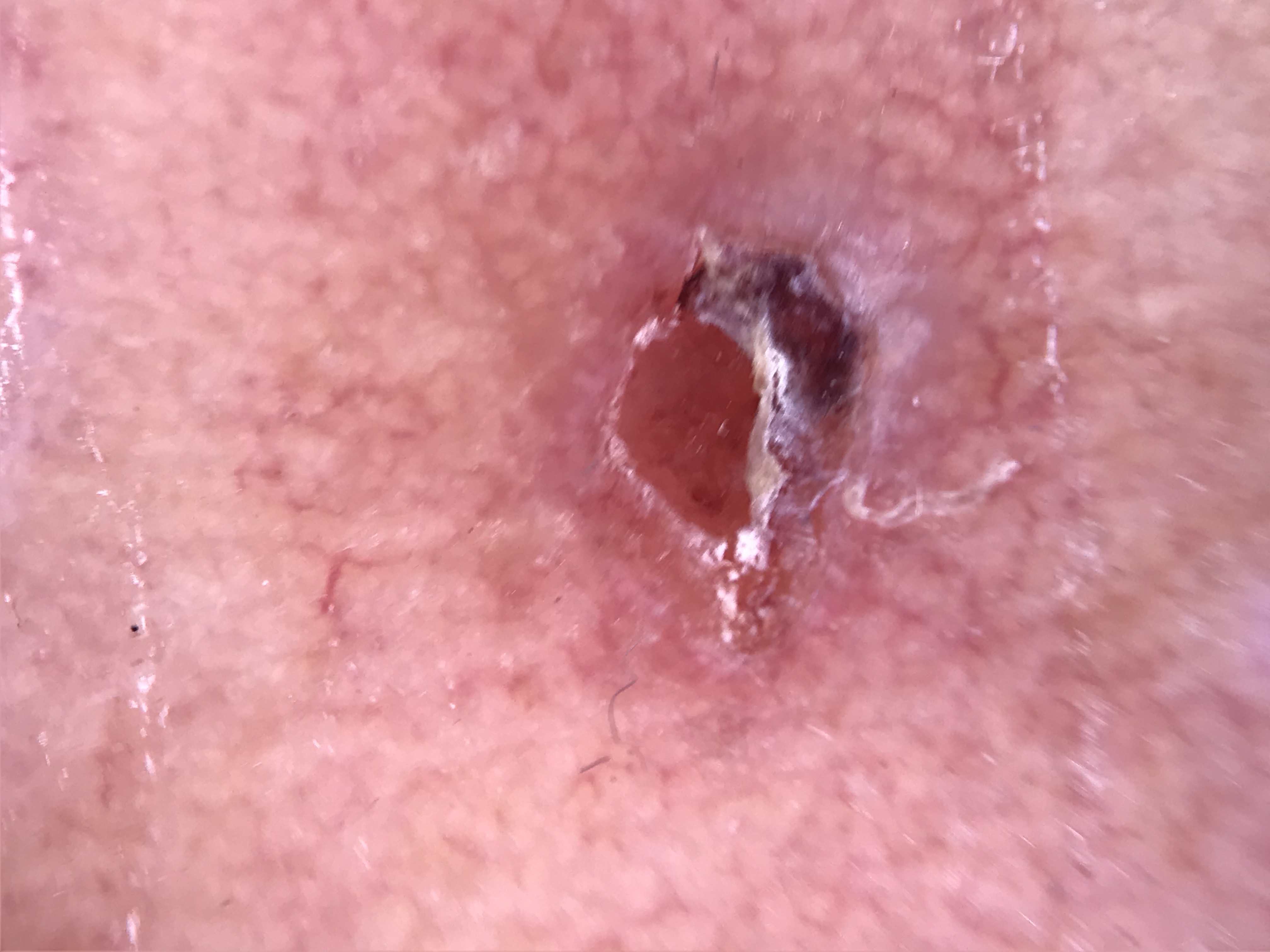Q: What kind of image is this?
A: dermatoscopy
Q: What is the diagnosis?
A: squamous cell carcinoma (biopsy-proven)